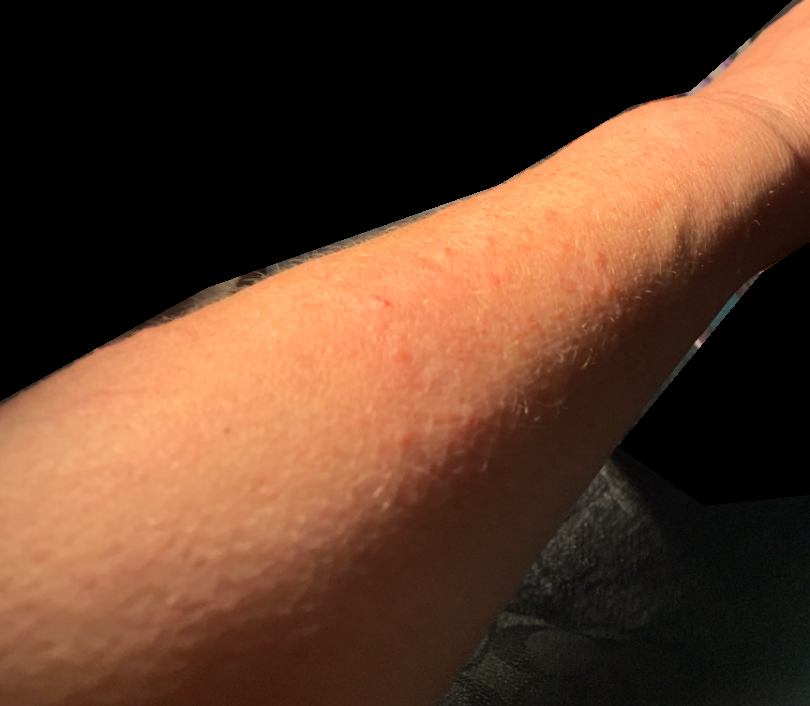History: No associated systemic symptoms reported. The contributor is female. The photo was captured at an angle. FST II; lay graders estimated Monk Skin Tone 2–3. The arm is involved. Present for less than one week. The patient described the issue as a rash. The patient reports the lesion is raised or bumpy. Impression: On teledermatology review, Contact dermatitis (40%); Allergic Contact Dermatitis (40%); Folliculitis (20%).